A dermoscopic close-up of a skin lesion.
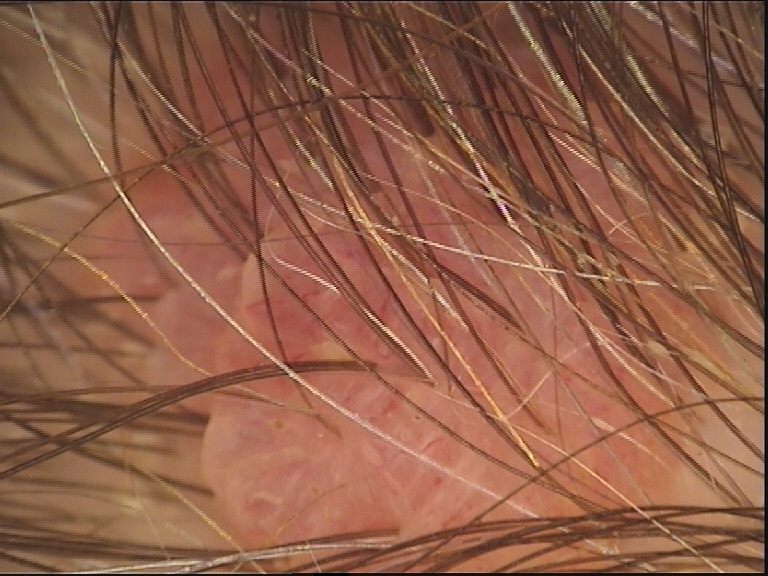Case:
– lesion type — banal
– label — dermal nevus (expert consensus)